The subject is a female aged 18–29 · the photograph was taken at an angle · the patient notes the lesion is raised or bumpy · skin tone: Fitzpatrick skin type III · reported lesion symptoms include burning and itching · the patient described the issue as a rash · the lesion involves the leg · present for less than one week: 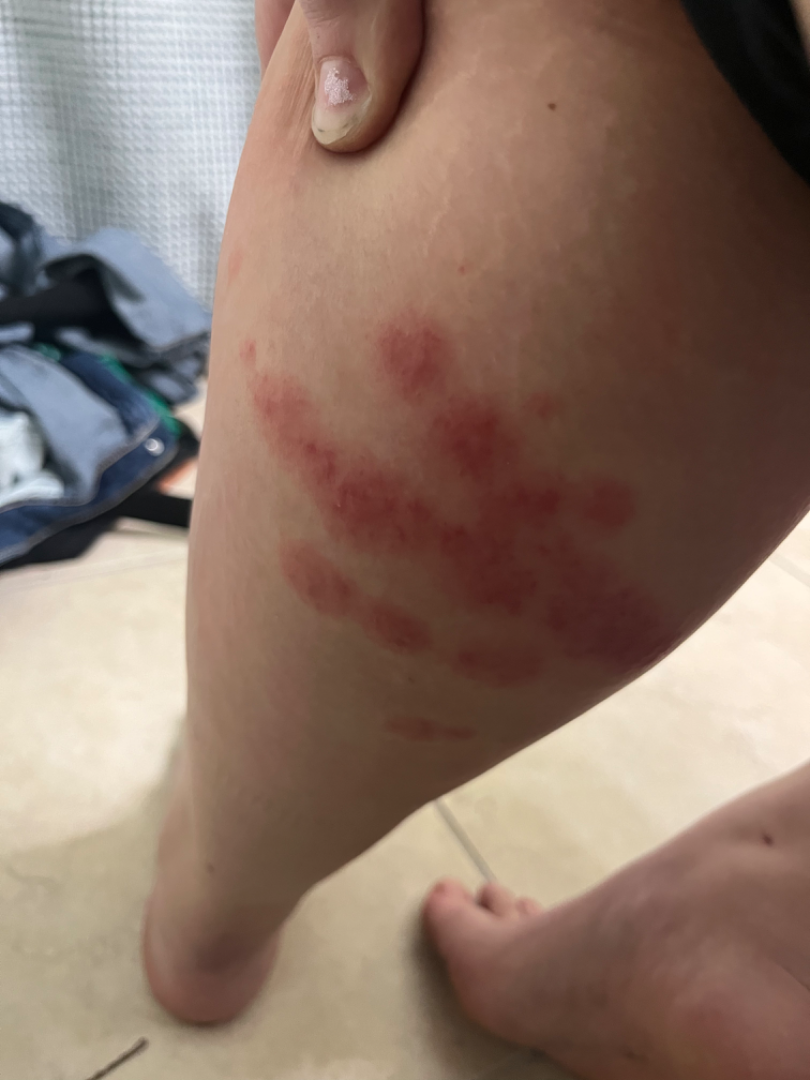The dermatologist could not determine a likely condition from the photograph alone.